A dermoscopic close-up of a skin lesion.
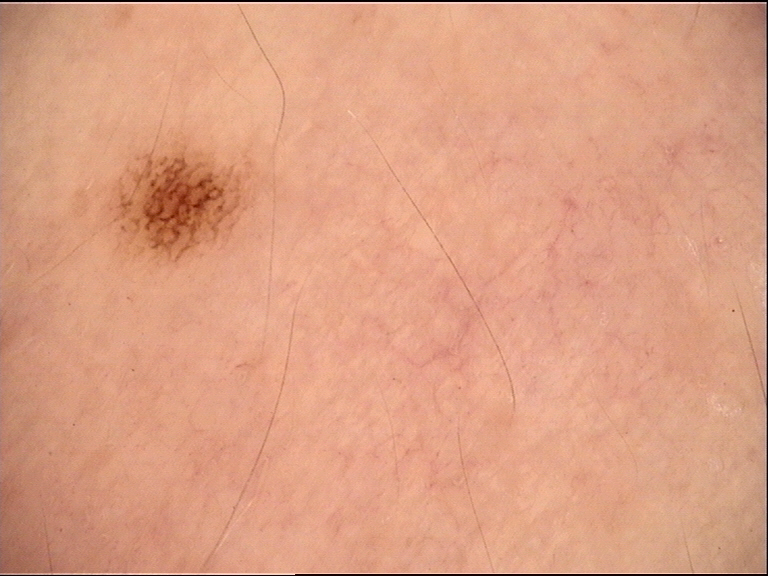* label · dysplastic junctional nevus (expert consensus)